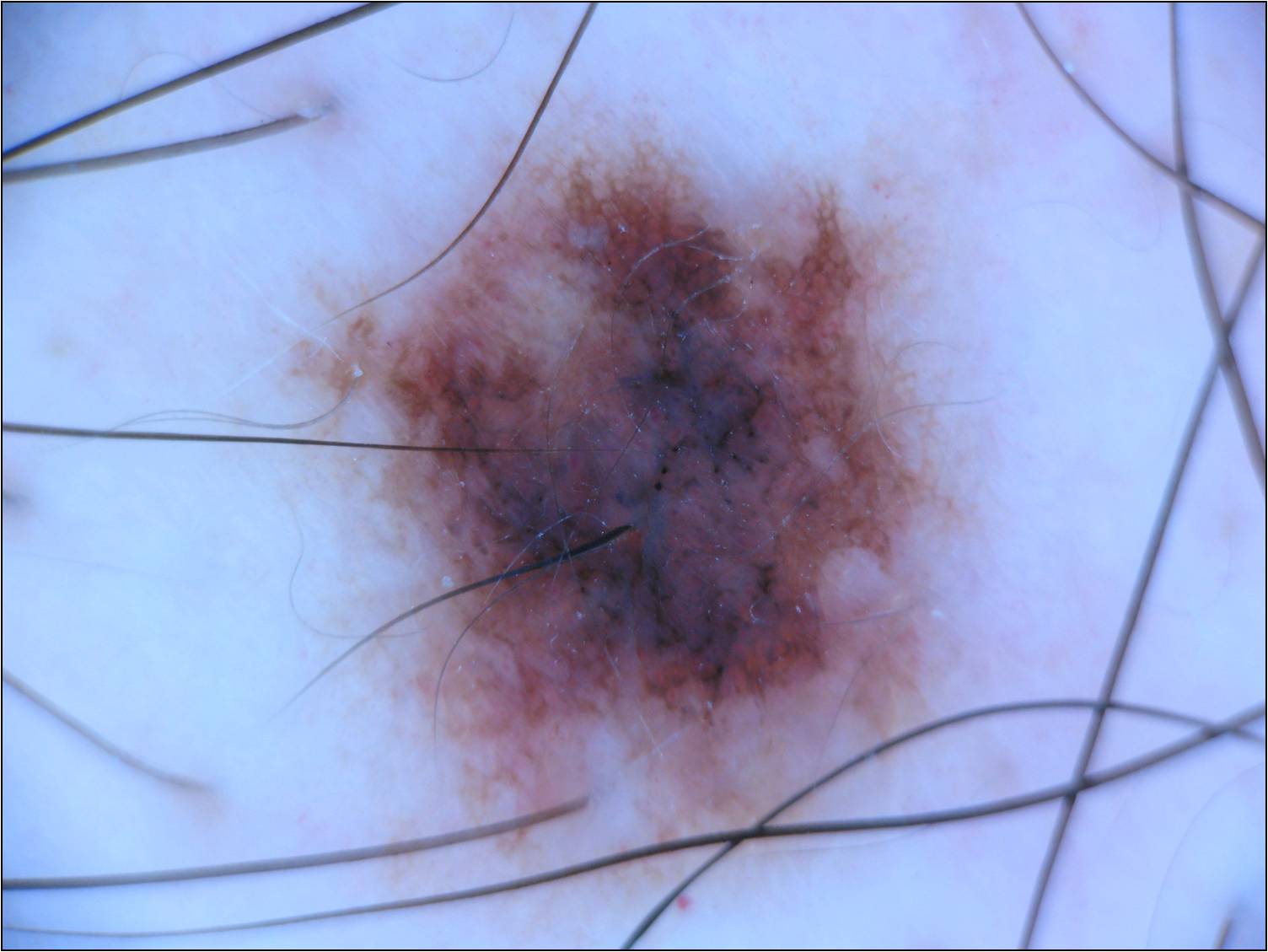Image and clinical context: A dermoscopic view of a skin lesion. A male patient aged 48-52. Lesion location: <box>265, 105, 980, 889</box>. Dermoscopy demonstrates globules and pigment network; no negative network, streaks, or milia-like cysts. Conclusion: Expert review diagnosed this as a melanocytic nevus.